A dermoscopic image of a skin lesion.
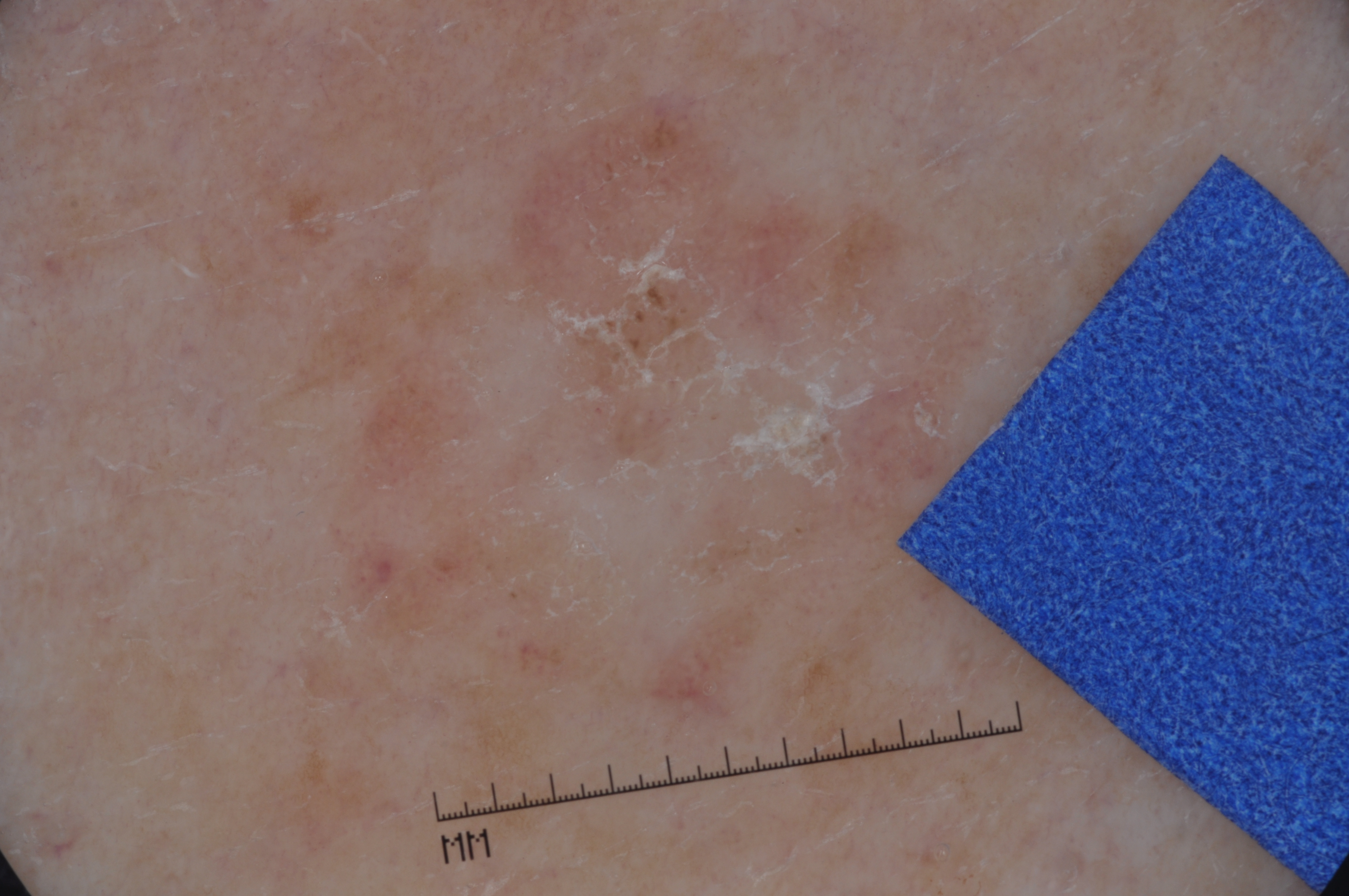Summary: Dermoscopic examination shows no pigment network, milia-like cysts, negative network, or streaks. The lesion is bounded by <bbox>358, 101, 988, 749</bbox>. A moderately sized lesion. Conclusion: The diagnostic assessment was a seborrheic keratosis.